This is a close-up image. Reported duration is one to four weeks. The patient described the issue as a rash. No relevant systemic symptoms. The contributor is female. The affected area is the arm. Symptoms reported: darkening, bothersome appearance, itching, burning, pain, enlargement and bleeding: 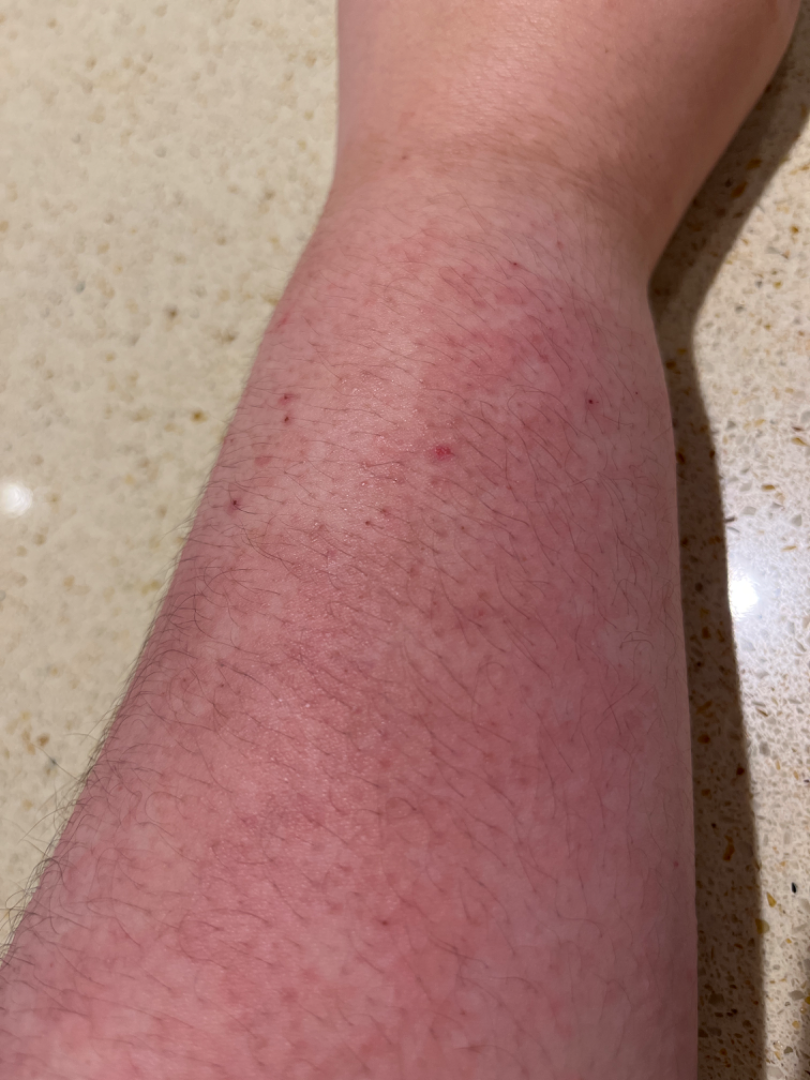Most likely Eczema; also raised was Allergic Contact Dermatitis; a more distant consideration is Acute dermatitis, NOS; less likely is Hypersensitivity; less probable is Viral Exanthem; lower on the differential is Contact dermatitis, NOS.